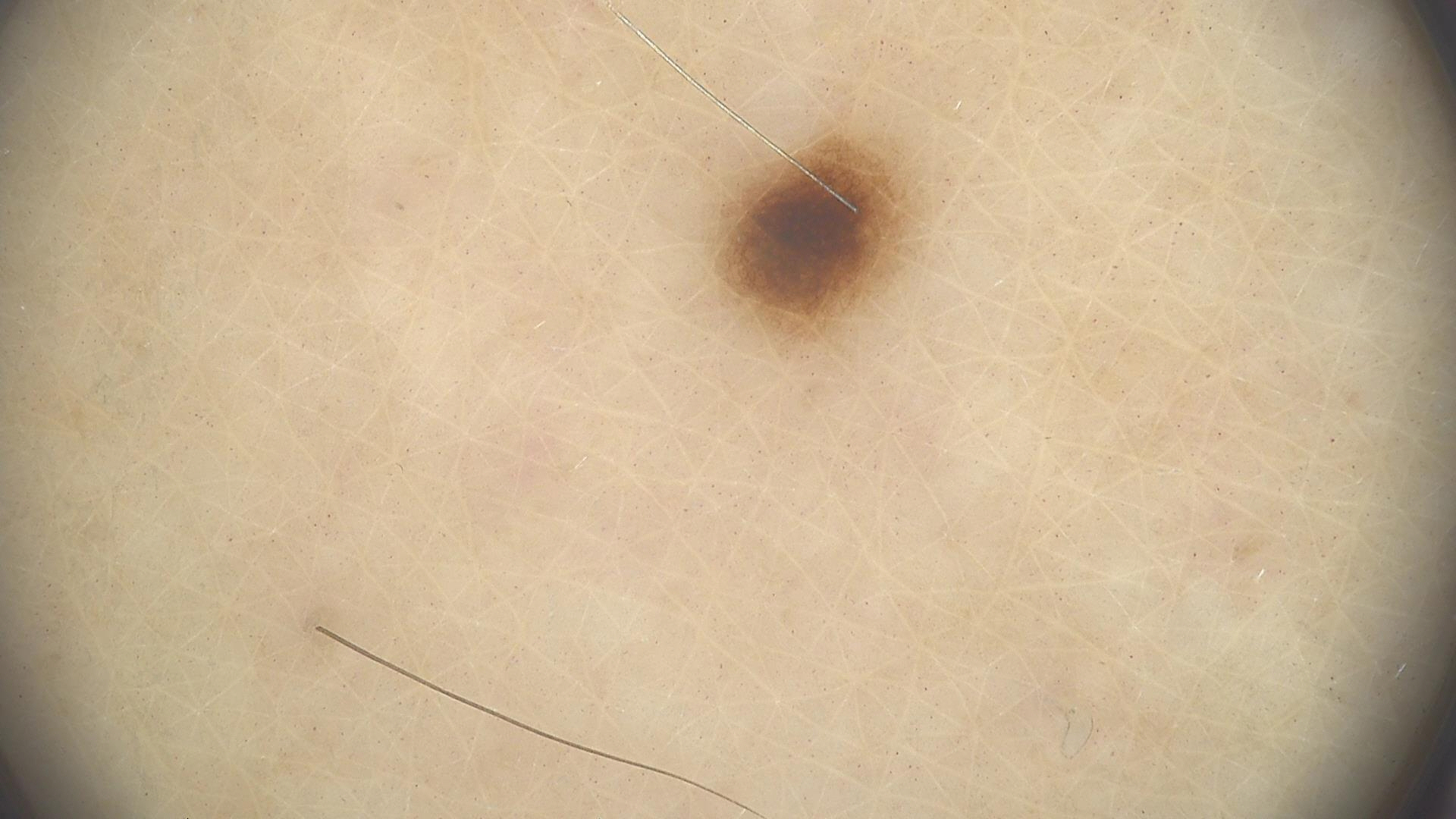image: dermatoscopy
diagnostic label: dysplastic junctional nevus (expert consensus)